Located on the arm · the contributor reports itching · reported duration is less than one week · a close-up photograph · the contributor reports the lesion is fluid-filled and raised or bumpy · self-categorized by the patient as skin that appeared healthy to them — 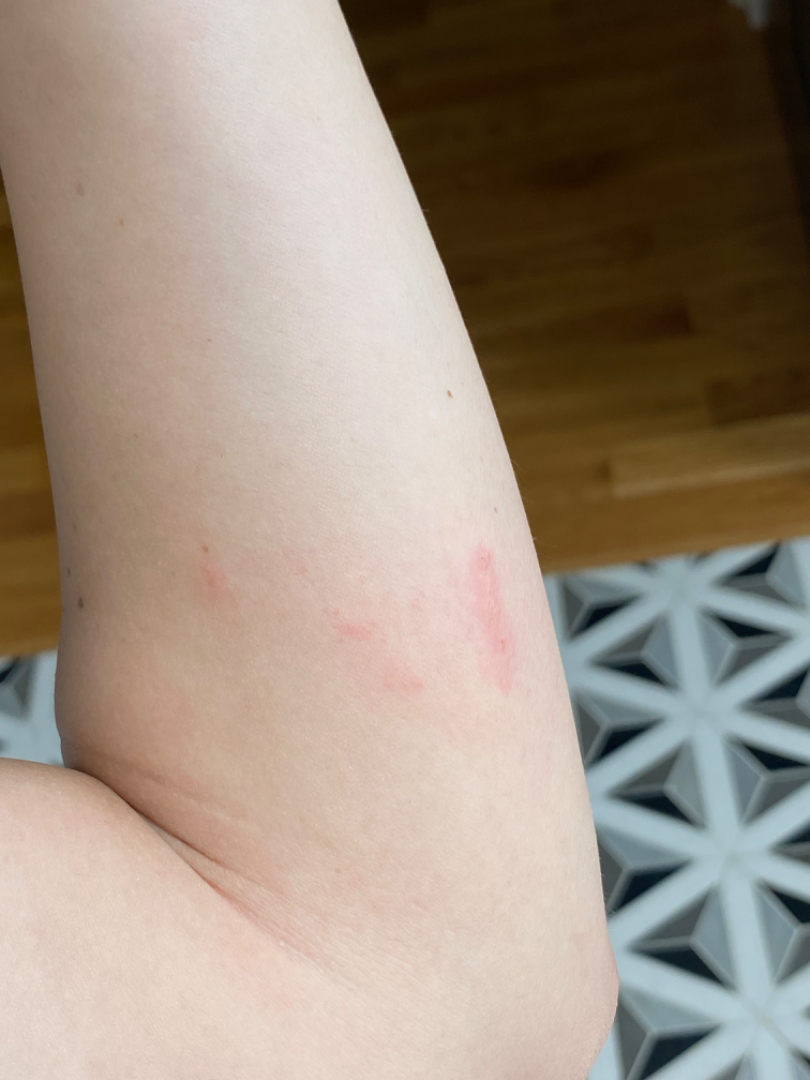| key | value |
|---|---|
| assessment | could not be assessed |